Fitzpatrick phototype III · the patient notes bothersome appearance and enlargement · the photo was captured at a distance · the arm and leg are involved · associated systemic symptoms include joint pain · self-categorized by the patient as a rash · the patient notes the lesion is raised or bumpy · male patient, age 40–49 — 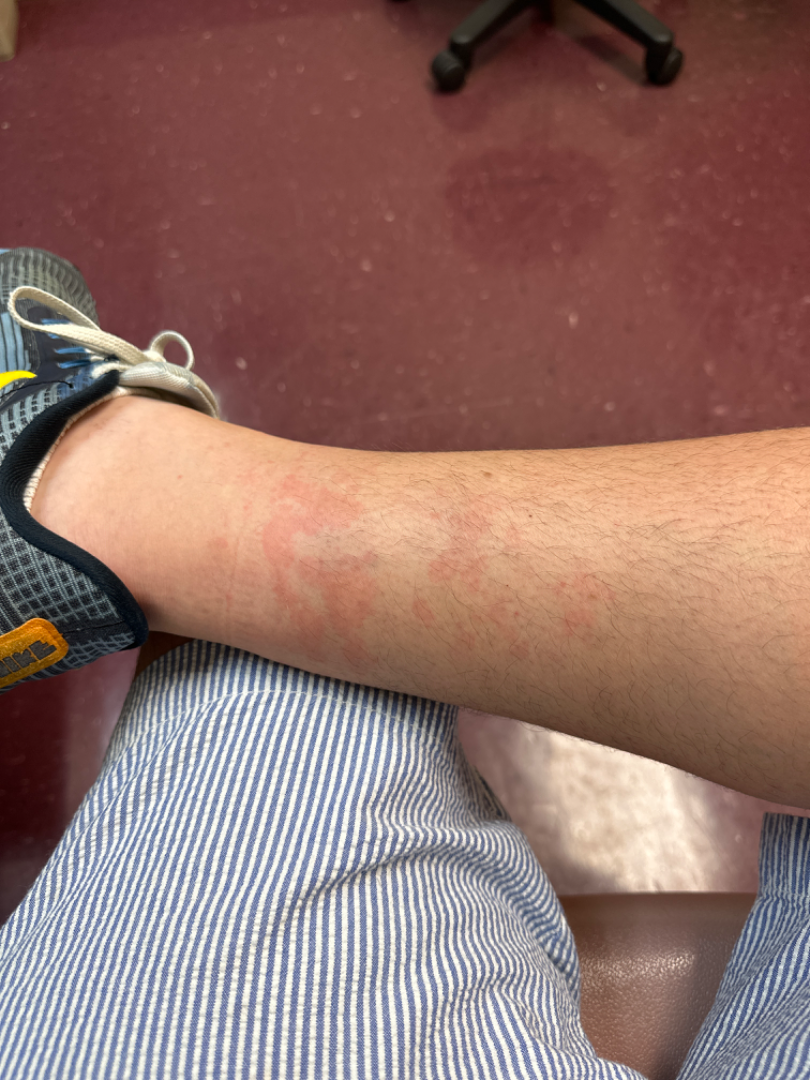The skin findings could not be characterized from the image.